The photograph was taken at a distance · FST II.
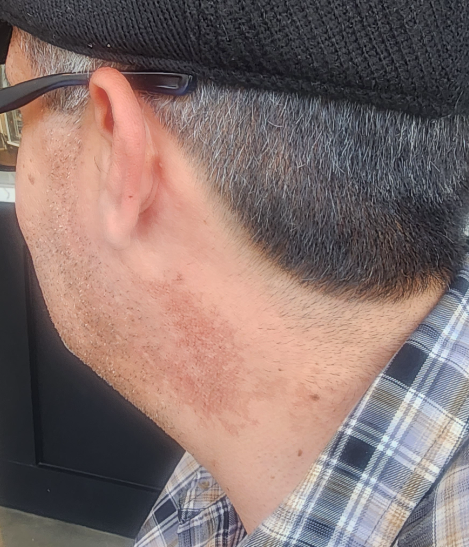differential:
  leading:
    - Poikiloderma
  considered:
    - Post-Inflammatory hyperpigmentation